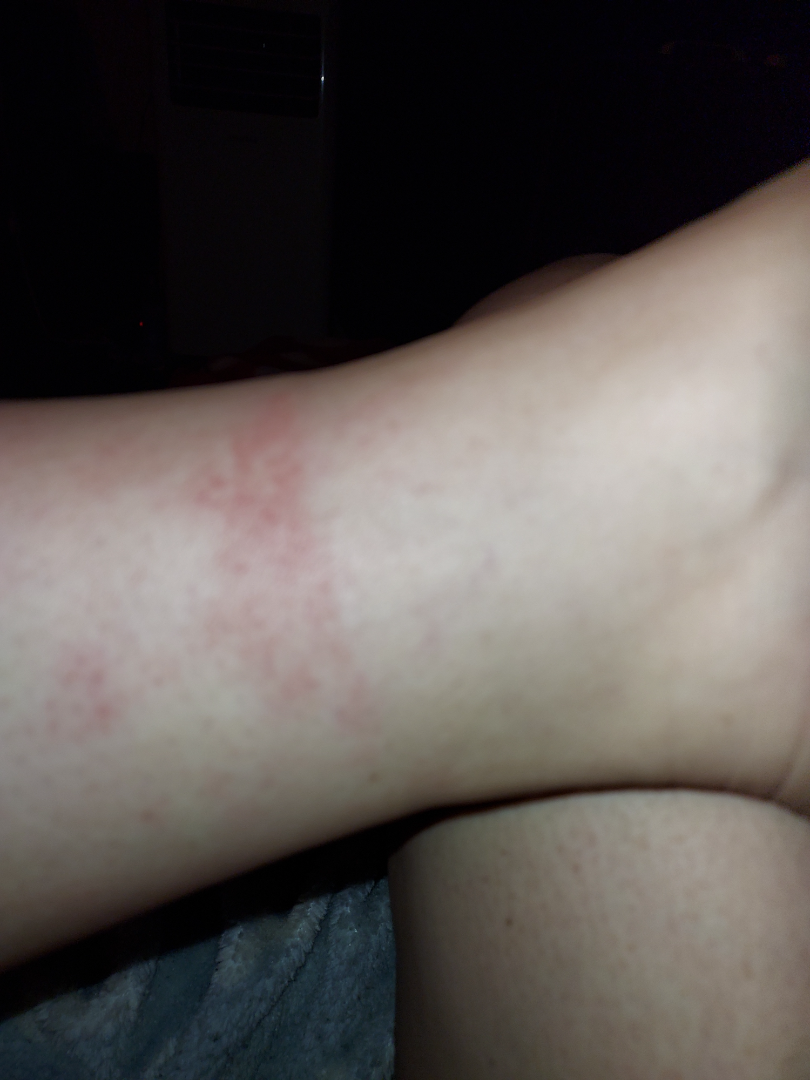Impression: The reviewer was unable to grade this case for skin condition. History: A close-up photograph. Skin tone: Fitzpatrick skin type III; human graders estimated Monk Skin Tone 1–2.